A dermoscopy image of a single skin lesion.
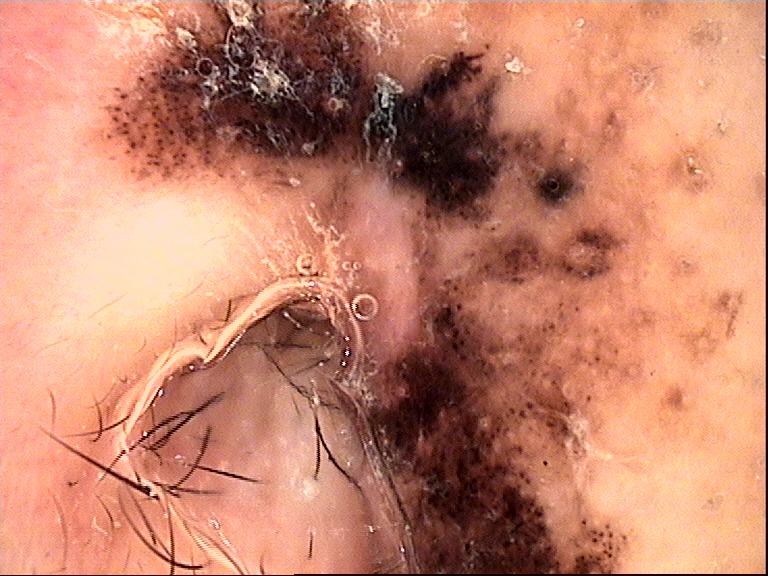The biopsy diagnosis was a skin cancer — a melanoma.